A contact-polarized dermoscopy image of a skin lesion · a male patient approximately 40 years of age — 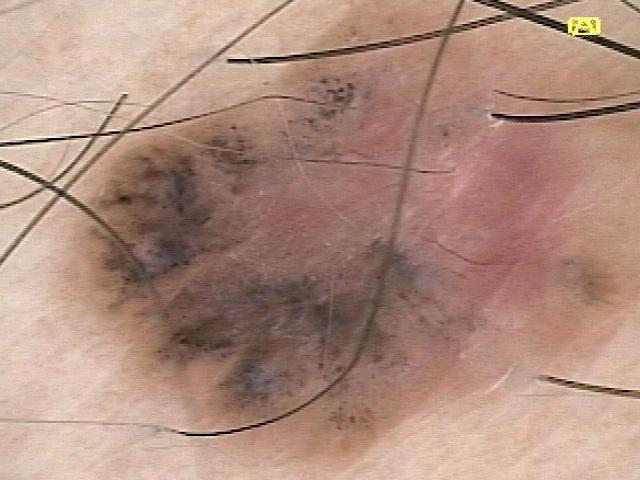Located on the trunk. On biopsy, the diagnosis was a basal cell carcinoma.